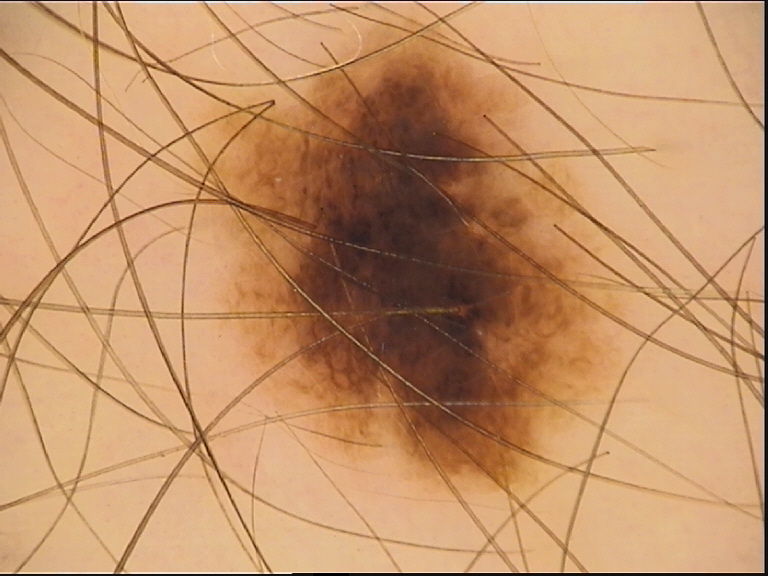| key | value |
|---|---|
| image type | dermatoscopy |
| assessment | dysplastic compound nevus (expert consensus) |